A skin lesion imaged with a dermatoscope.
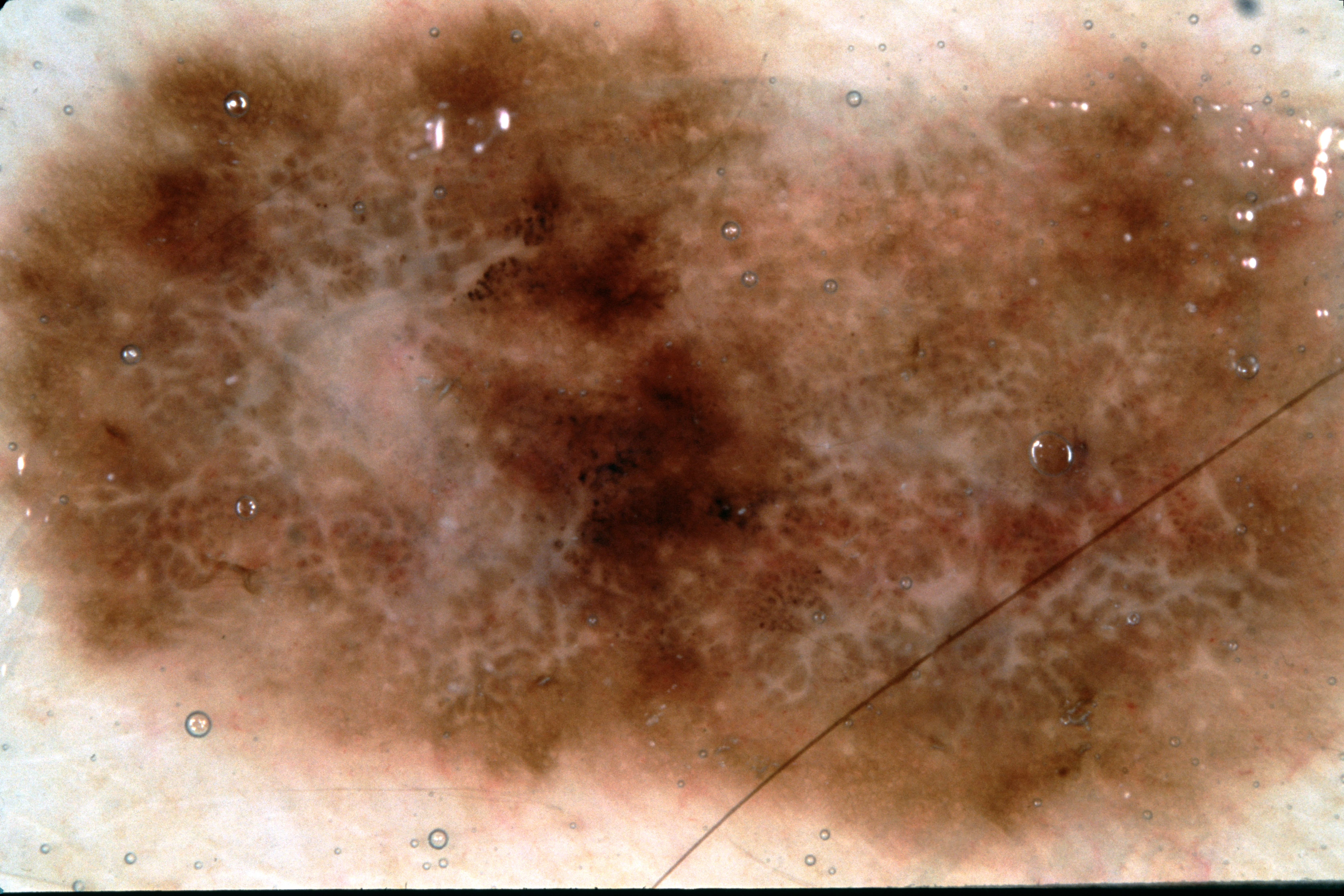  lesion_location: spans the dermoscopic field
  dermoscopic_features:
    present:
      - pigment network
      - negative network
    absent:
      - milia-like cysts
      - streaks
  diagnosis:
    name: melanoma
    malignancy: malignant
    lineage: melanocytic
    provenance: histopathology